The lesion involves the arm; the photograph was taken at a distance:
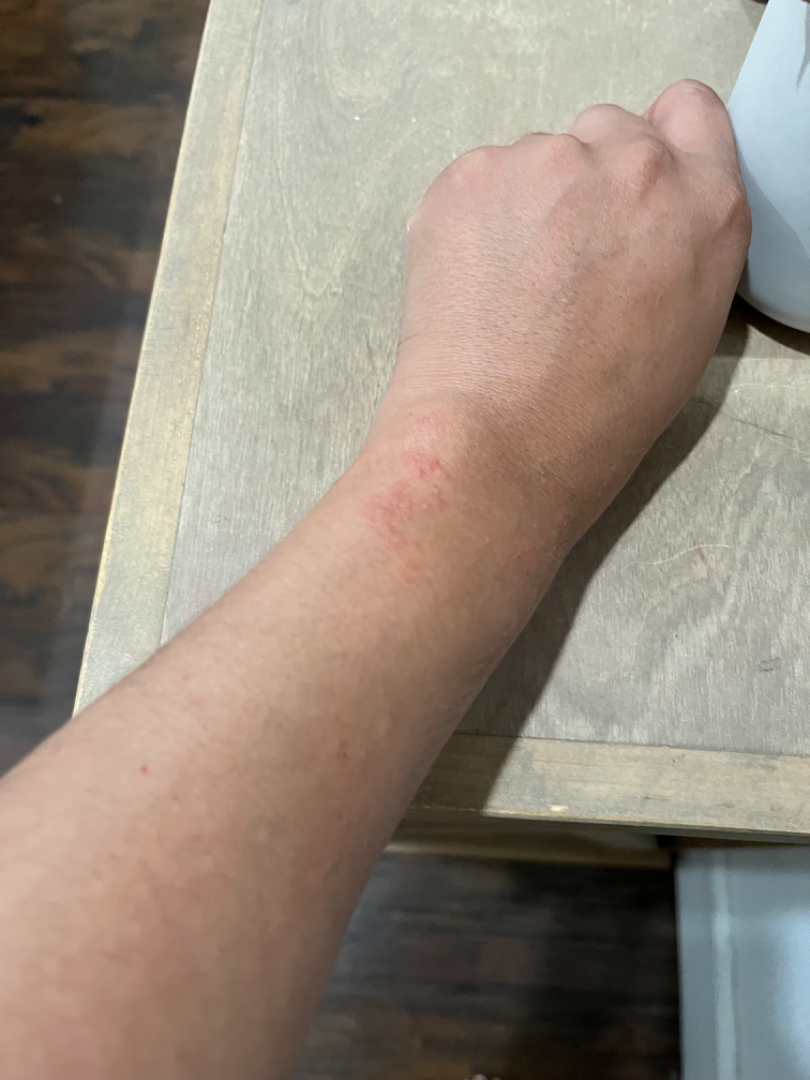{
  "skin_tone": {
    "fitzpatrick": "V",
    "monk_skin_tone": [
      2,
      3
    ]
  },
  "systemic_symptoms": "none reported",
  "duration": "less than one week",
  "texture": "raised or bumpy",
  "differential": {
    "leading": [
      "Allergic Contact Dermatitis"
    ],
    "considered": [
      "Irritant Contact Dermatitis"
    ]
  }
}